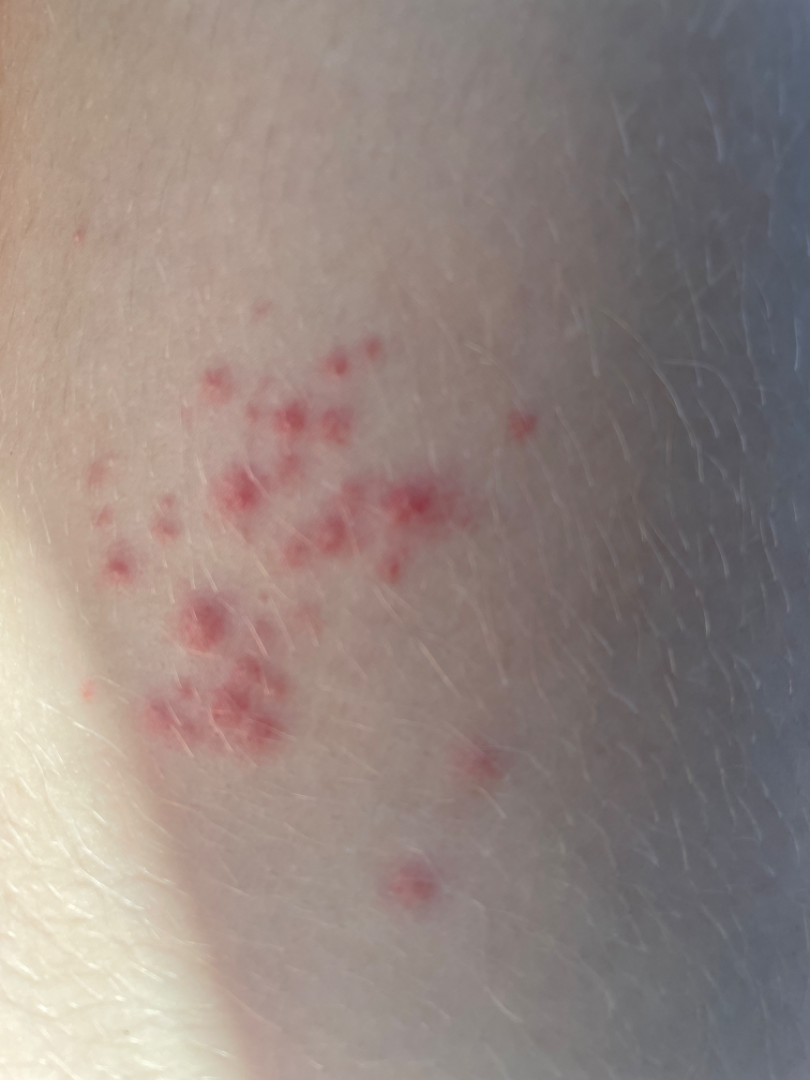history: about one day | photo taken: close-up | symptoms: bothersome appearance, itching, pain and burning | body site: leg | dermatologist impression: Folliculitis, Herpes Zoster and Herpes Simplex were considered with similar weight.